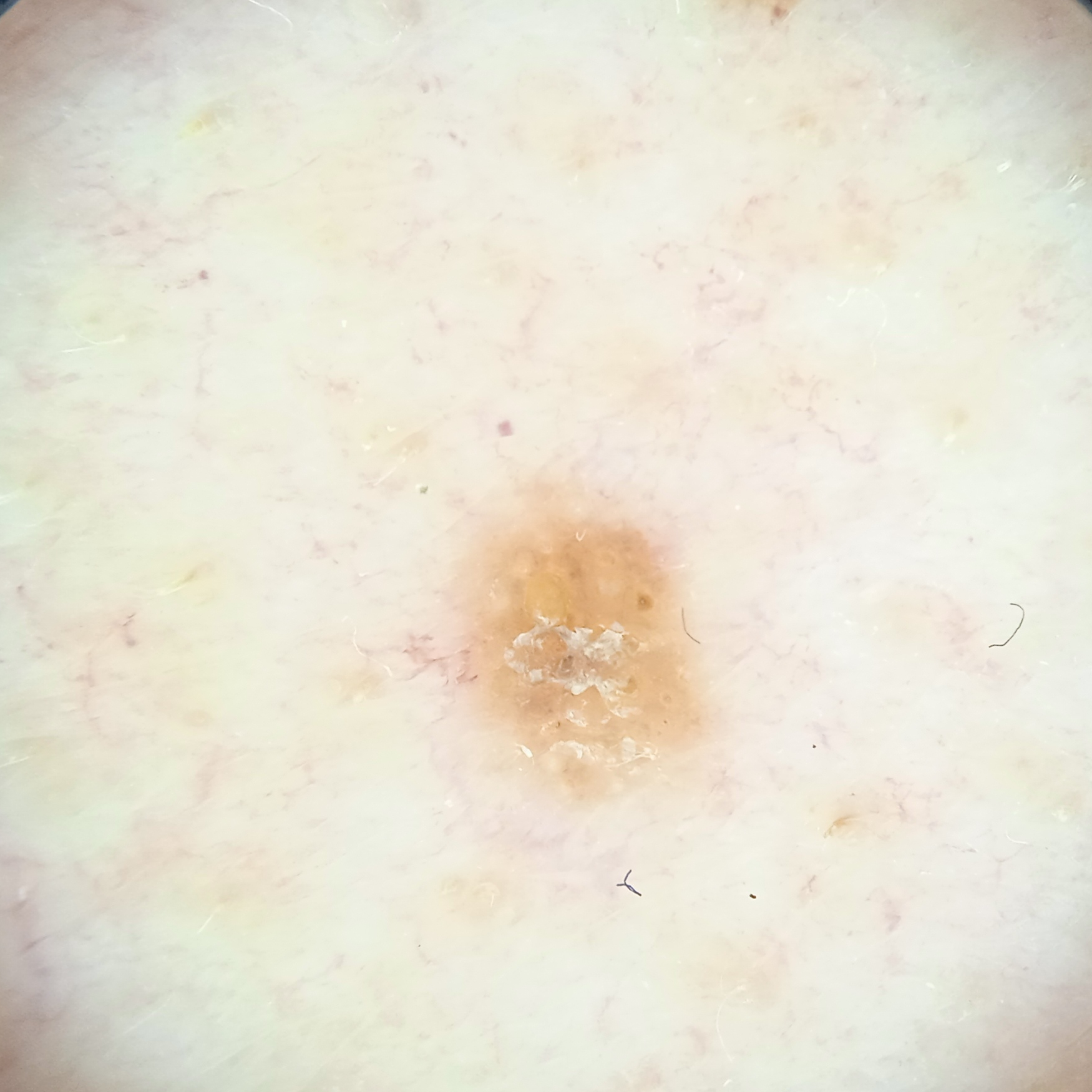| field | value |
|---|---|
| nevus count | numerous melanocytic nevi |
| subject | male, aged 65 |
| clinical context | research study (no referral diagnosis) |
| image type | dermatoscopic image |
| relevant history | a personal history of skin cancer, a family history of skin cancer, immunosuppression |
| sun reaction | skin reddens painfully with sun exposure |
| body site | the back |
| lesion size | 3.3 mm |
| diagnostic label | seborrheic keratosis (dermatologist consensus) |